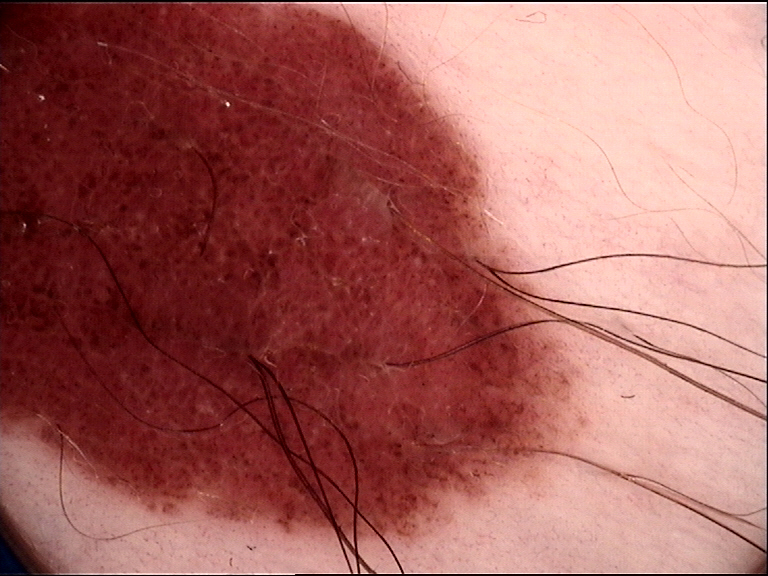A dermoscopic image of a skin lesion. The diagnosis was a banal lesion — a congenital compound nevus.